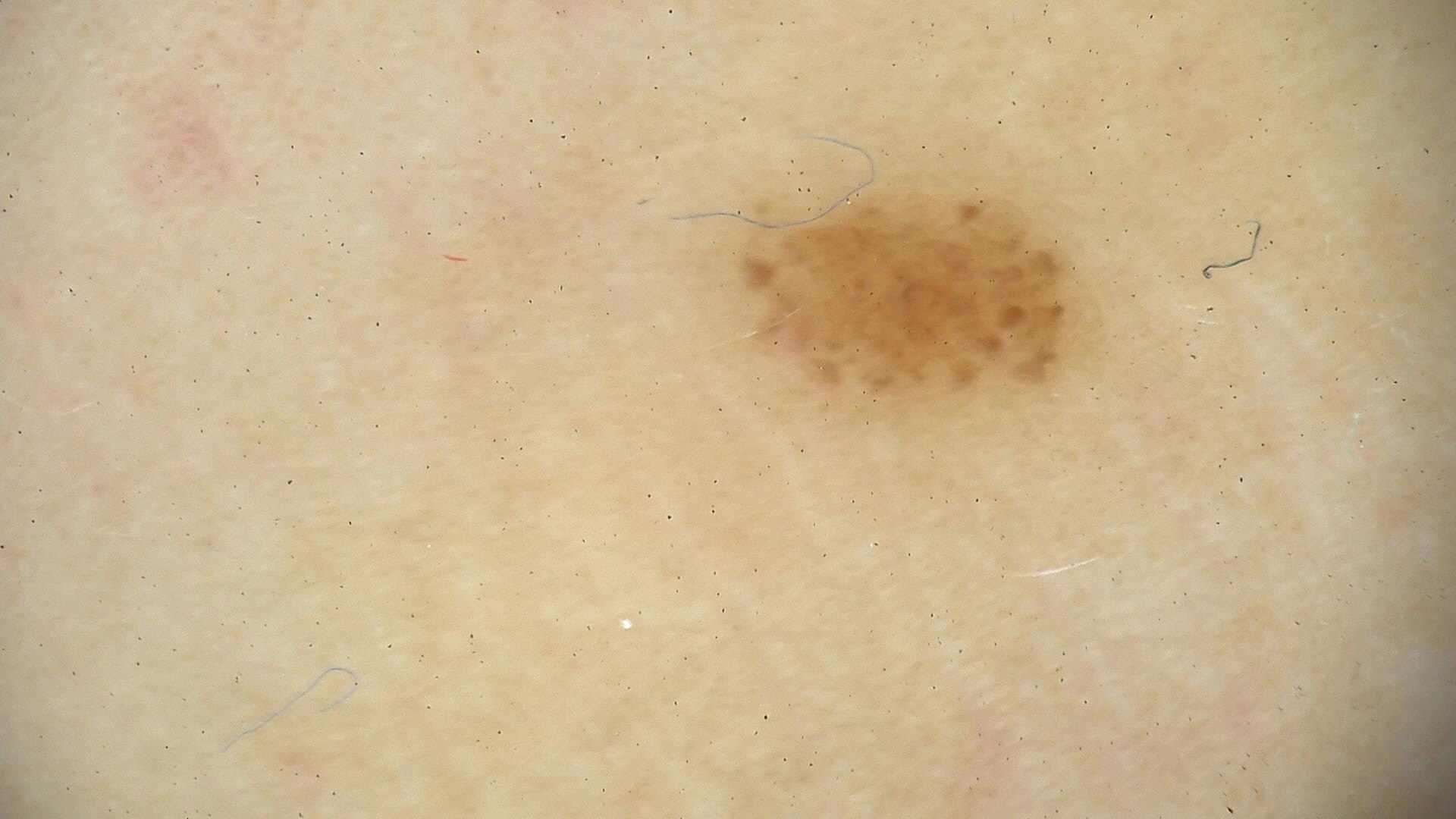The diagnostic label was a benign lesion — a dysplastic junctional nevus.